A skin lesion imaged with a dermatoscope: 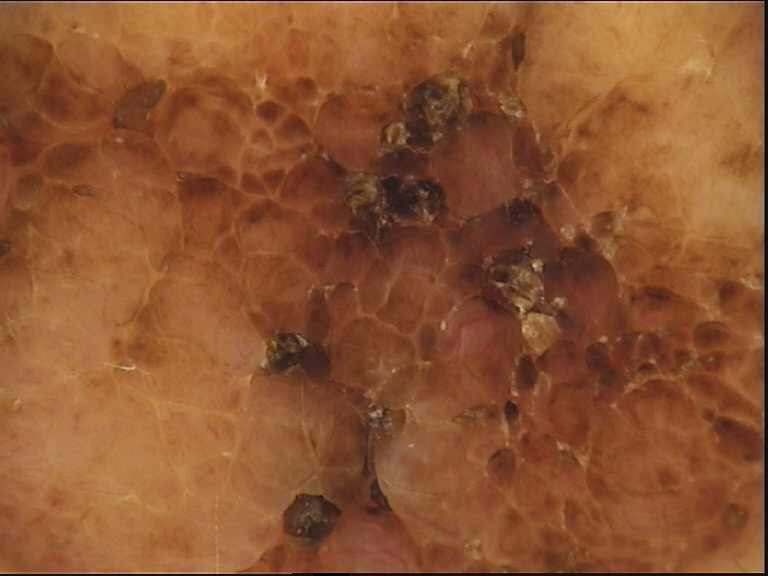label: dermal nevus (expert consensus).